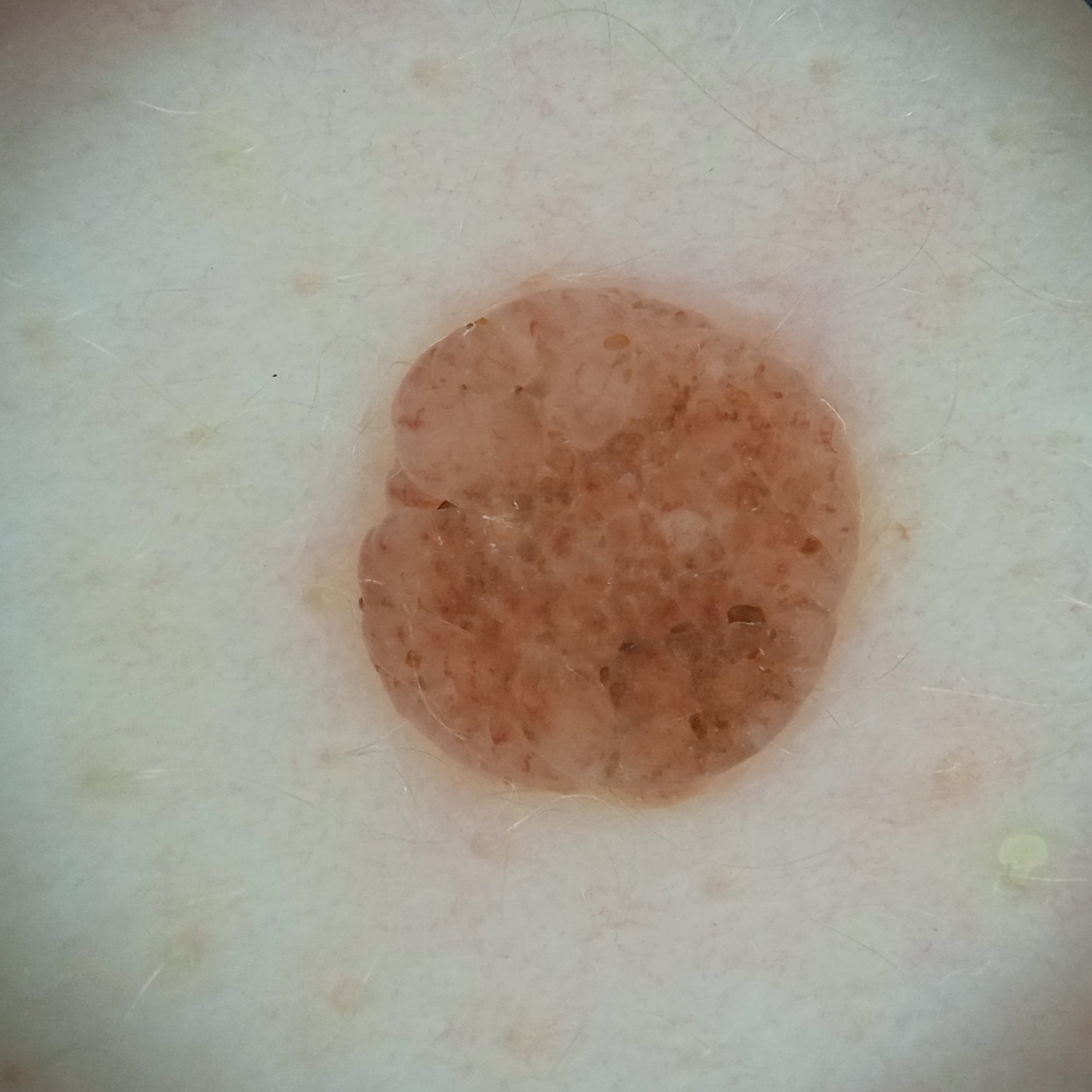patient=female, age 26; sun reaction=skin reddens with sun exposure; referral context=research study (no referral diagnosis); site=the back; lesion size=5.6 mm; assessment=melanocytic nevus (dermatologist consensus).